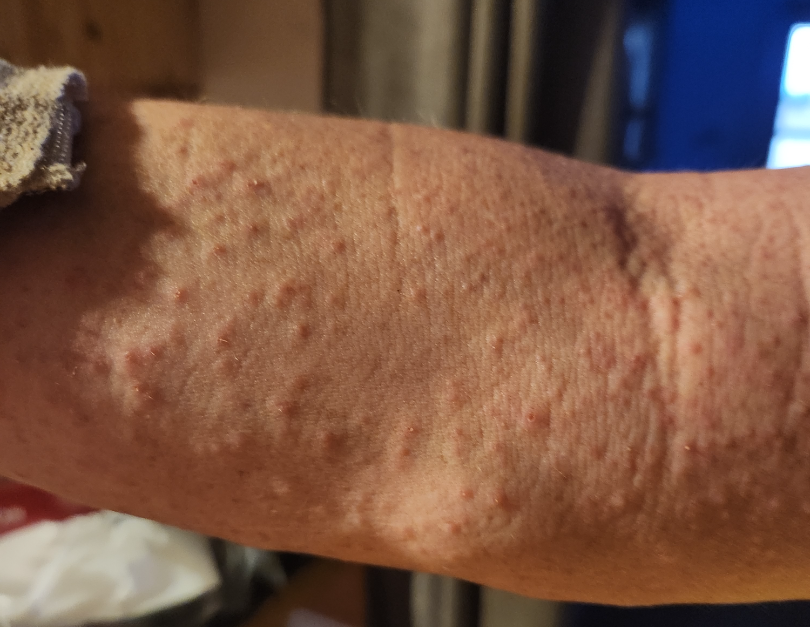Close-up view. The affected area is the arm. On remote dermatologist review, the differential includes Eczema, Scabies and Folliculitis, with no clear leading consideration.